Collected as part of a research study, without a referral diagnosis. A moderate number of moles by the patient's own estimate. By self-report, a personal history of cancer, a personal history of skin cancer, no immunosuppression, and no family history of skin cancer — 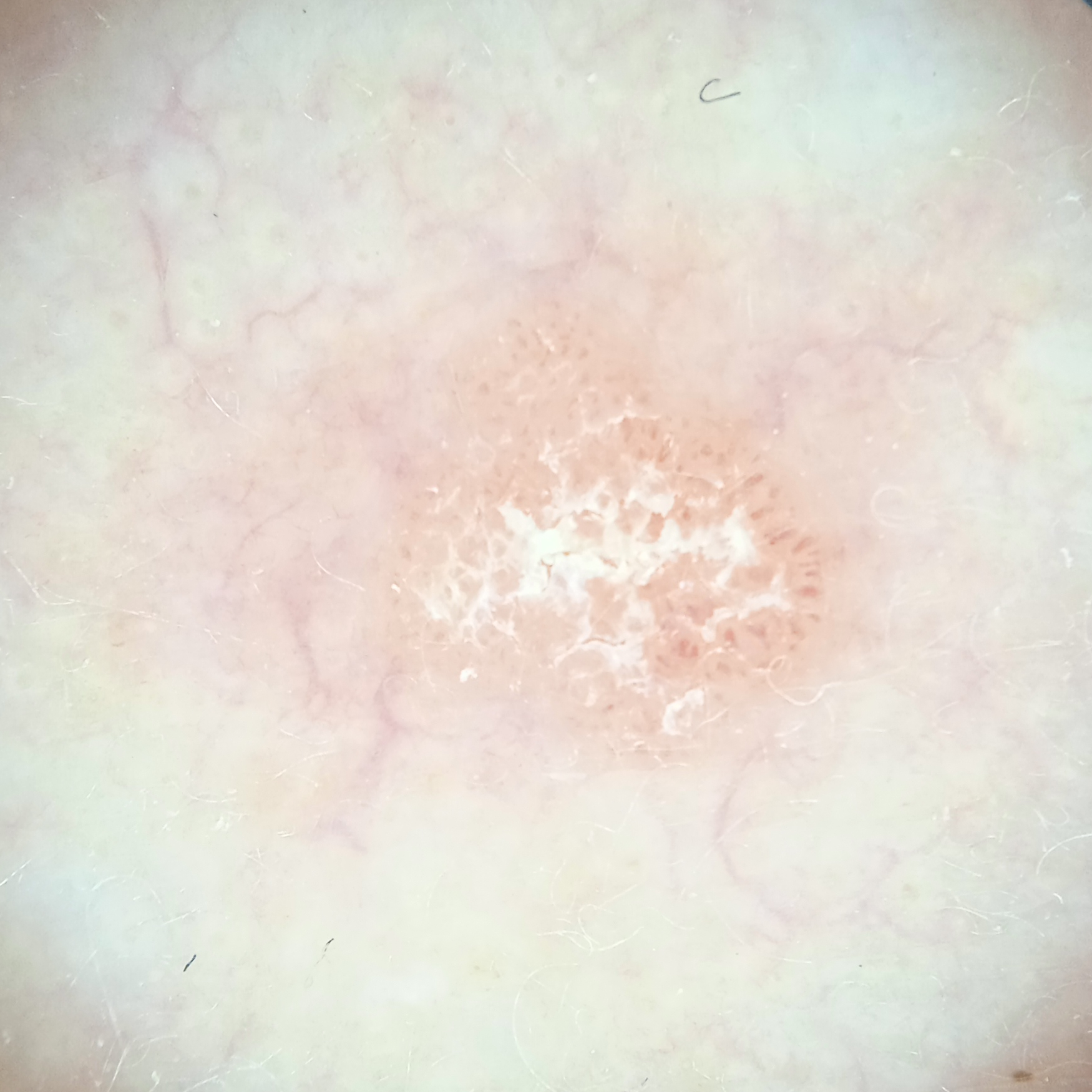lesion size: 4.3 mm | diagnosis: actinic keratosis (dermatologist consensus).